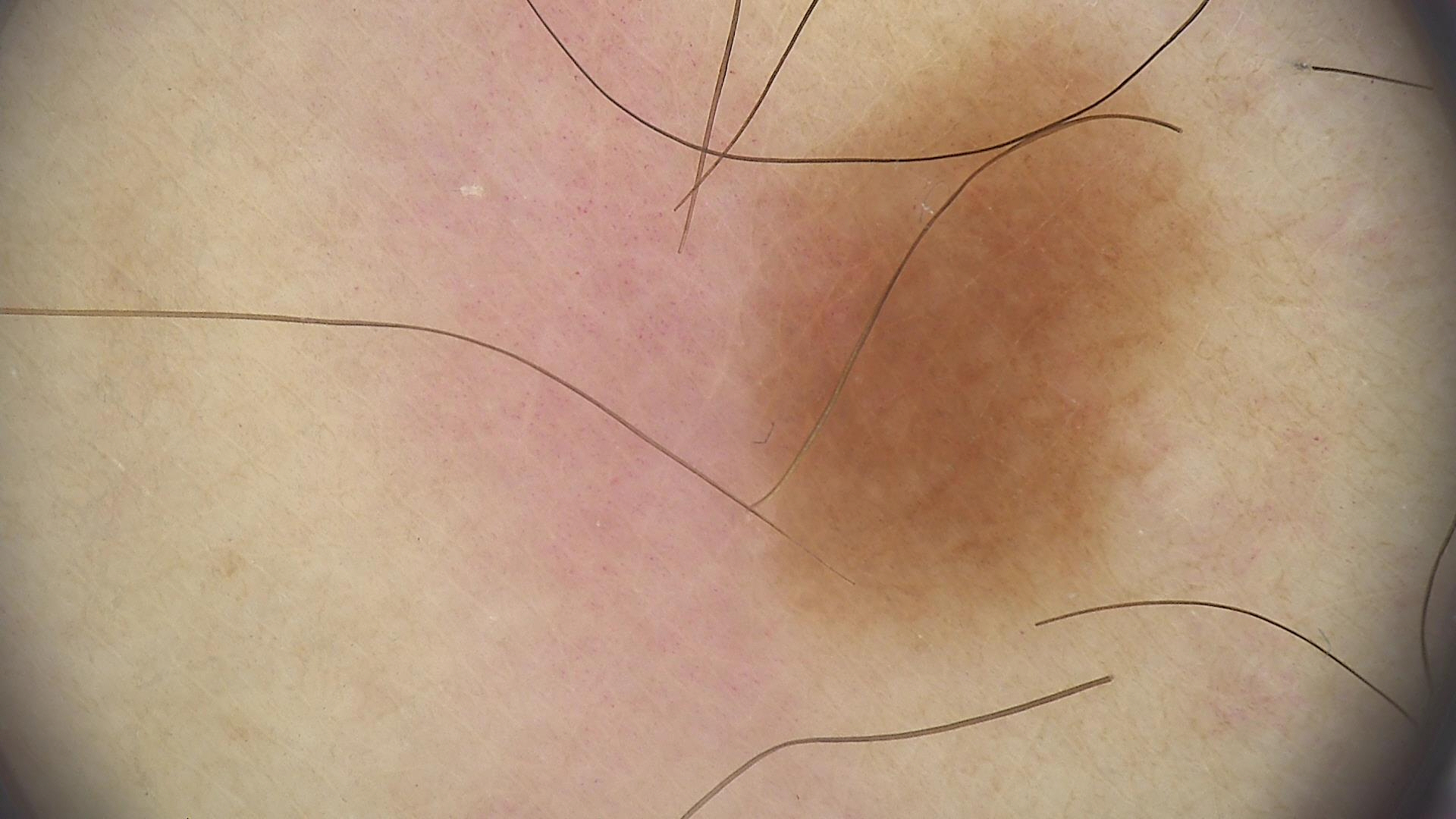– category: banal
– class: junctional nevus (expert consensus)